Dermoscopy of a skin lesion.
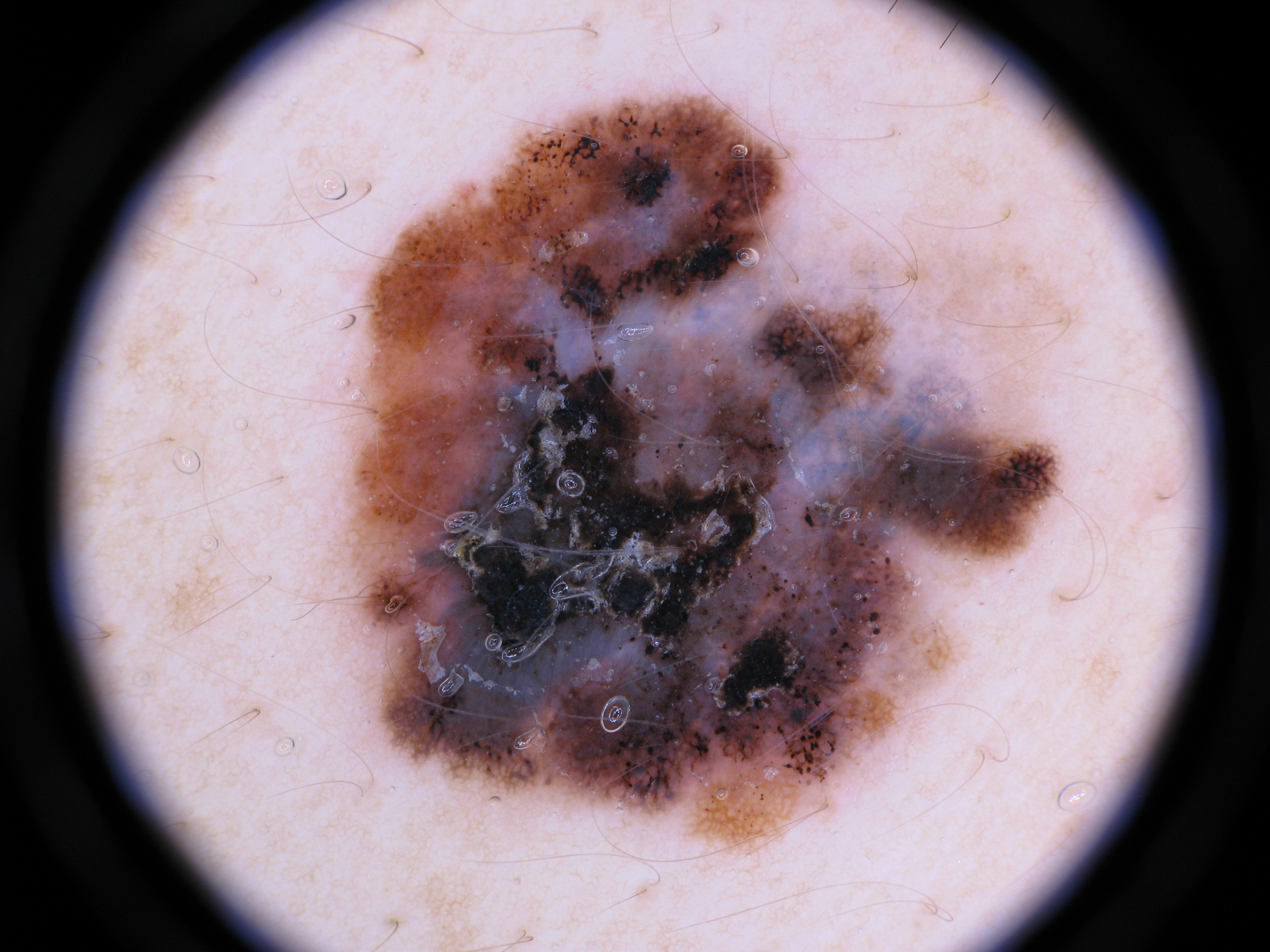With coordinates (x1, y1, x2, y2), the lesion occupies the region bbox(336, 91, 1090, 856). On dermoscopy, the lesion shows globules and pigment network. Histopathologically confirmed as a melanoma, a skin cancer.